History notes prior malignancy (patient or family) and prior skin cancer (patient or family) · a female subject in their teens · the patient is Fitzpatrick phototype I · a clinical photograph showing a skin lesion:
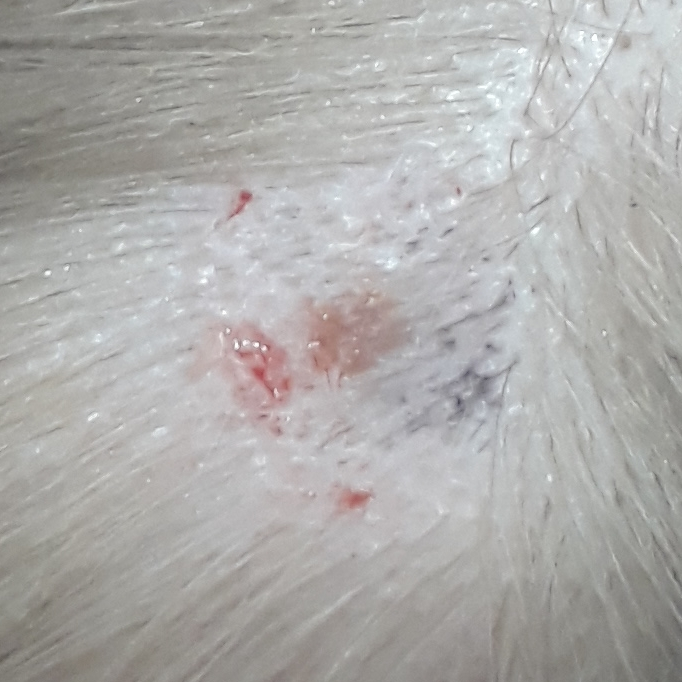Q: What are the lesion's dimensions?
A: 4x3 mm
Q: What symptoms does the patient report?
A: no itching
Q: What is this lesion?
A: nevus (biopsy-proven)